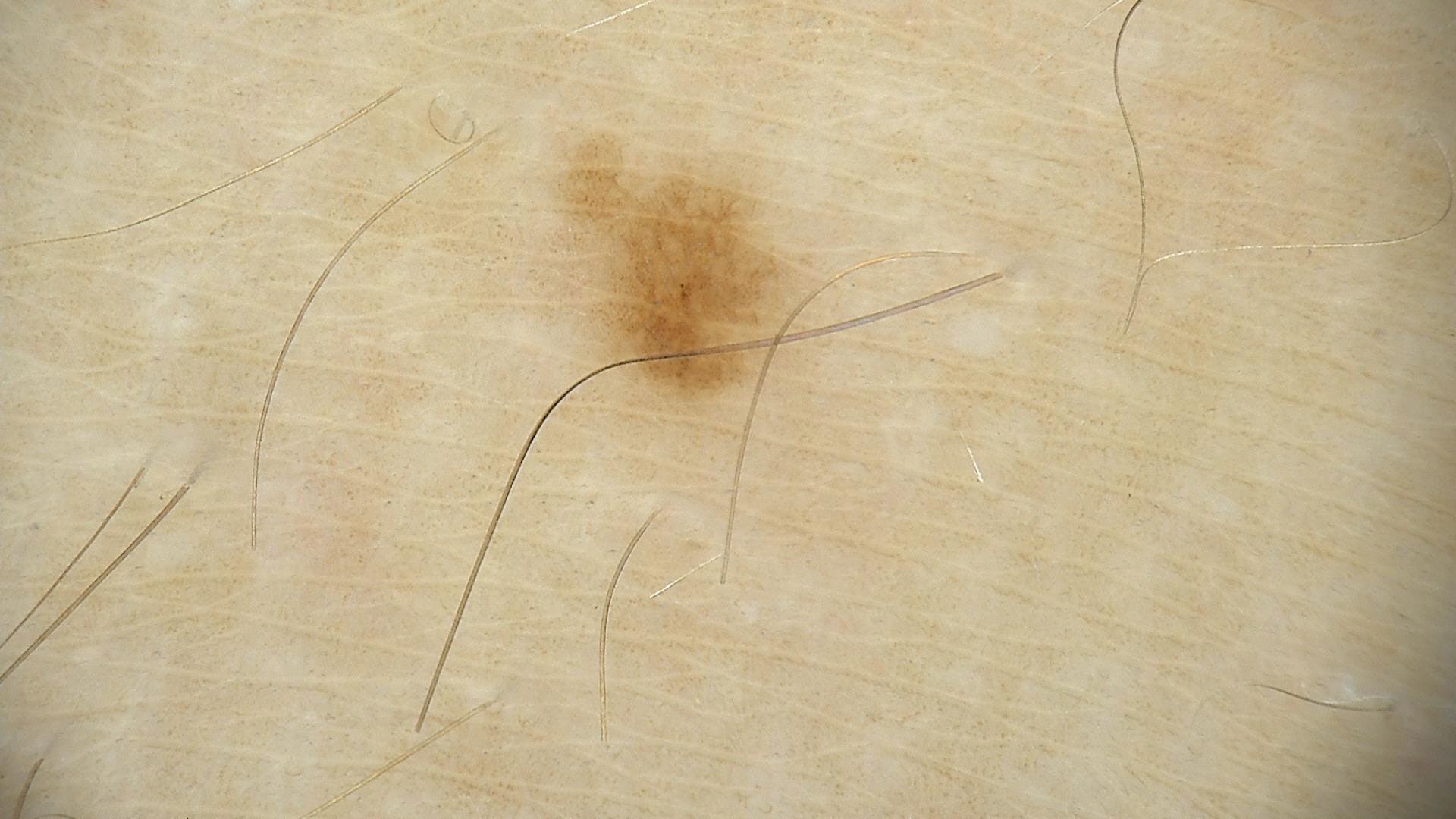The diagnosis was a benign lesion — a dysplastic junctional nevus.